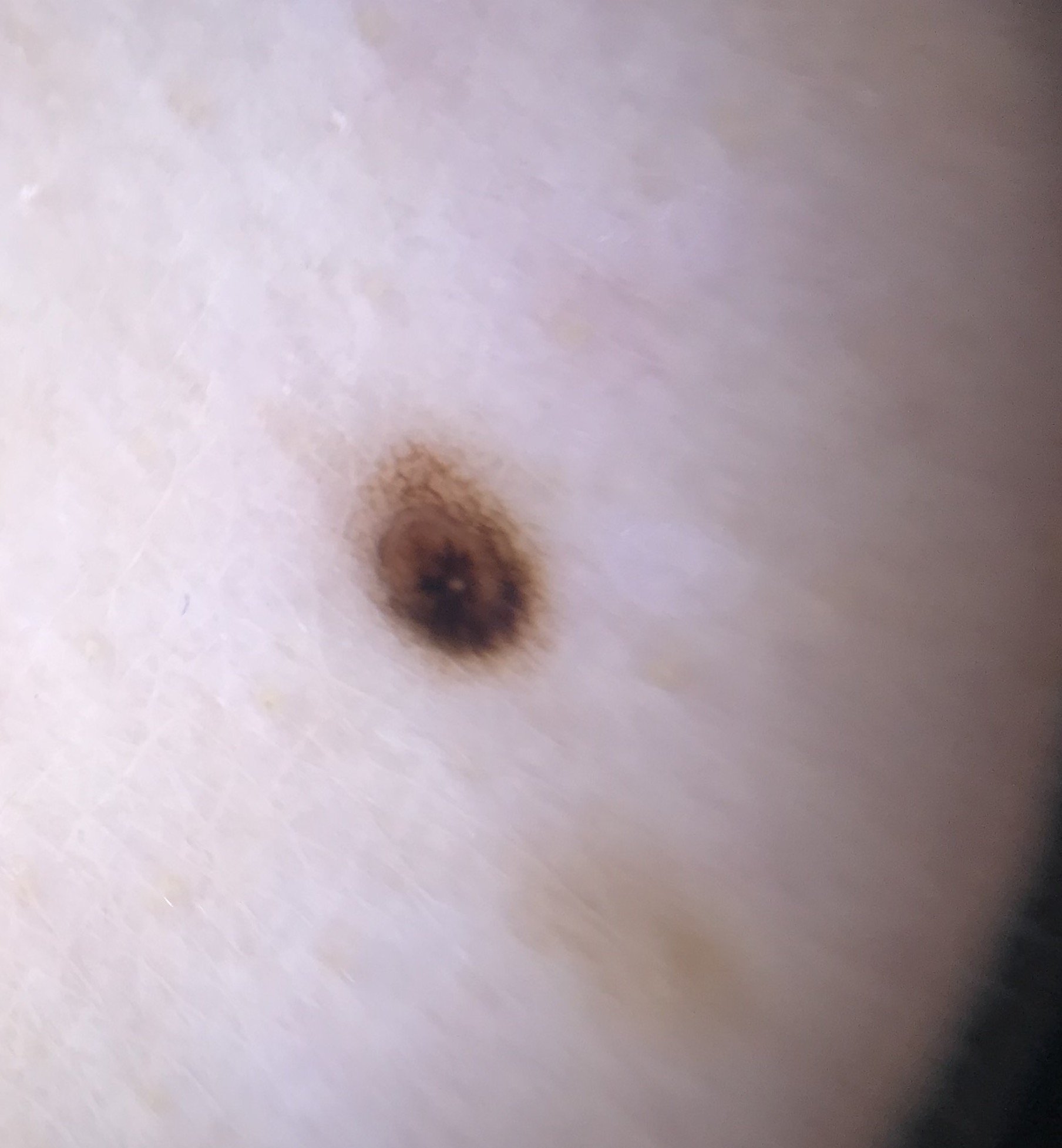Q: What kind of image is this?
A: dermatoscopy
Q: What is the diagnosis?
A: dysplastic compound nevus (expert consensus)